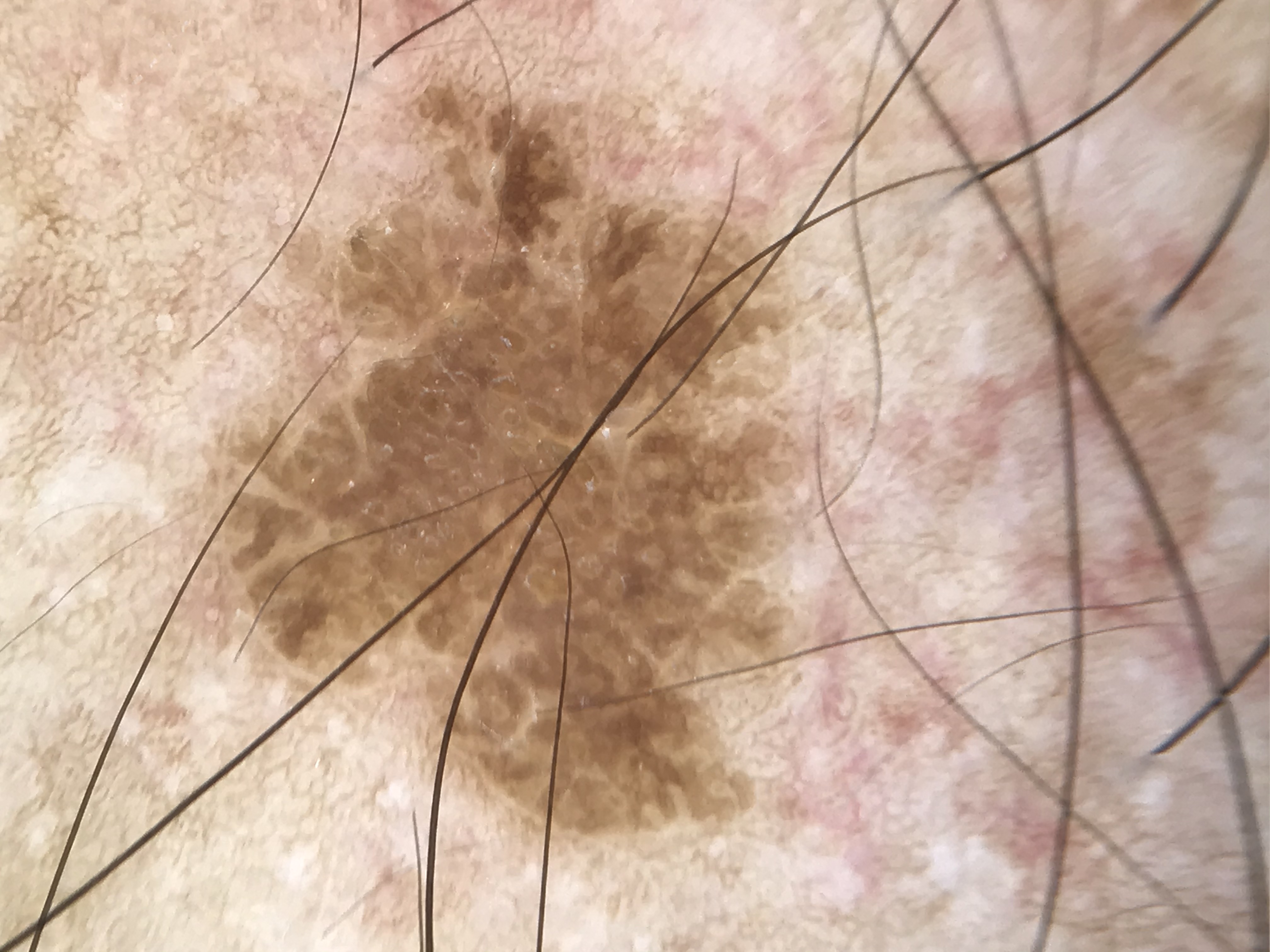<lesion>
<lesion_type>
<main_class>keratinocytic</main_class>
</lesion_type>
<diagnosis>
<name>seborrheic keratosis</name>
<code>sk</code>
<malignancy>benign</malignancy>
<super_class>non-melanocytic</super_class>
<confirmation>expert consensus</confirmation>
</diagnosis>
</lesion>